The patient is female, texture is reported as rough or flaky, the photograph was taken at an angle, the patient described the issue as a rash, skin tone: Fitzpatrick III.
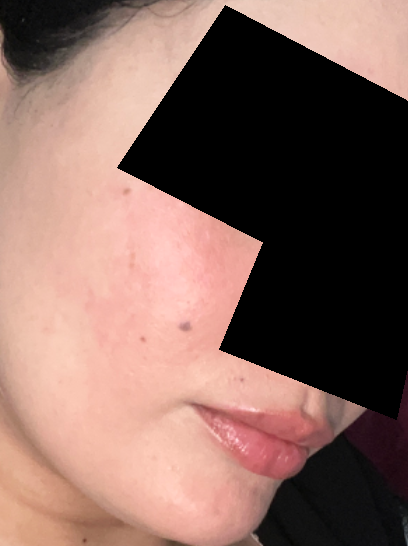Q: What was the assessment?
A: no skin condition identified